The photograph was taken at an angle: 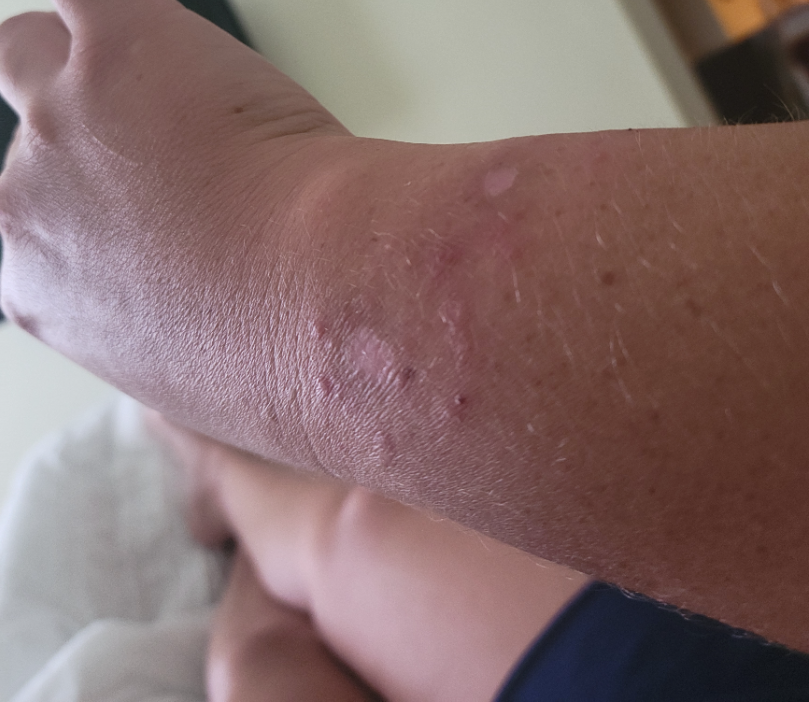{"differential": {"leading": ["Allergic Contact Dermatitis"], "considered": ["Acute and chronic dermatitis"]}}